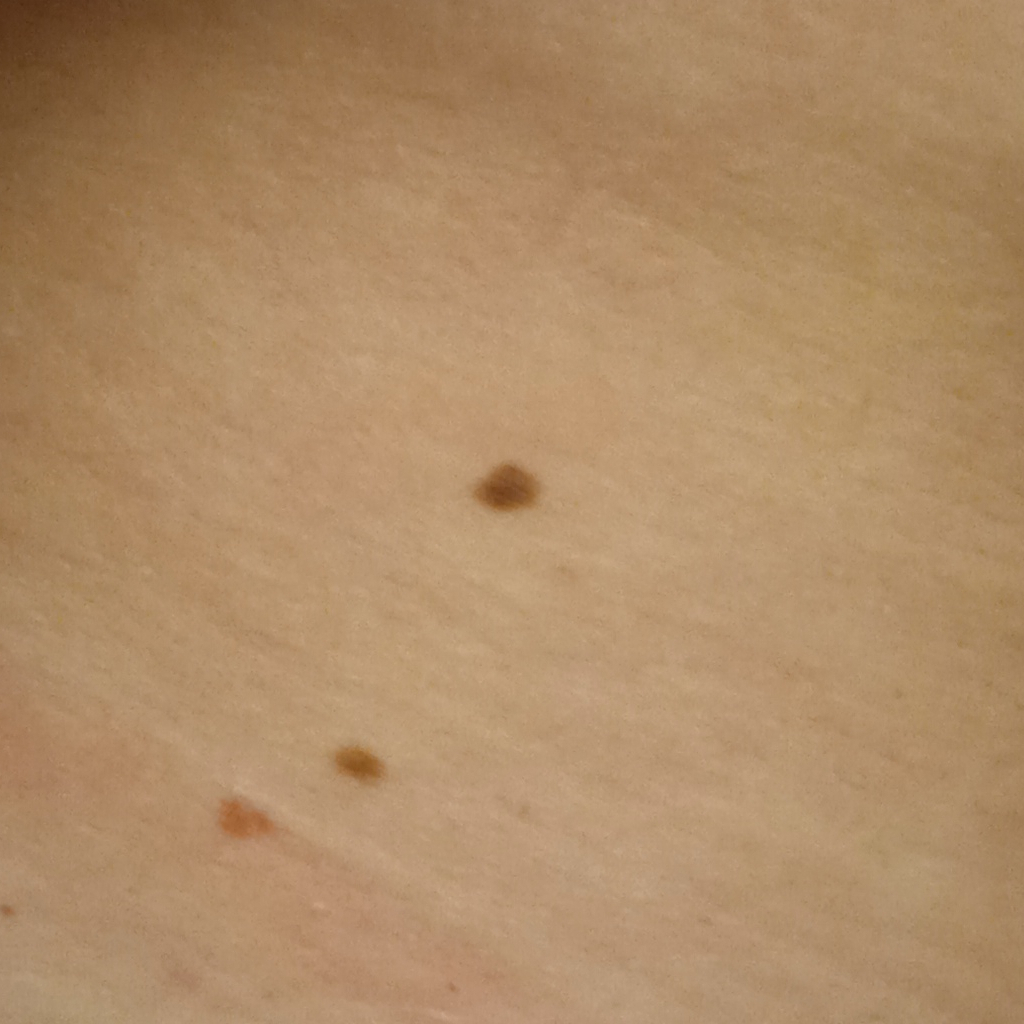Conclusion: The lesion was assessed as a melanocytic nevus.